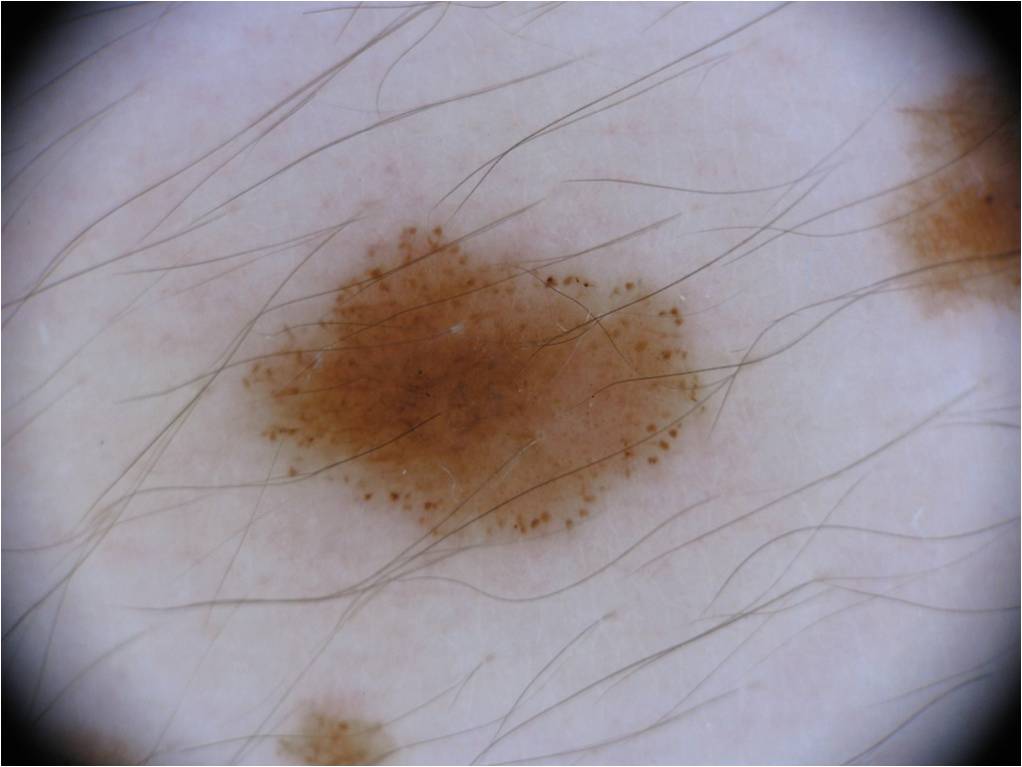Image and clinical context: This is a dermoscopic photograph of a skin lesion. A female subject approximately 15 years of age. As (left, top, right, bottom), the visible lesion spans bbox(242, 224, 704, 543). Dermoscopic review identifies pigment network and globules, with no negative network, milia-like cysts, or streaks. Impression: Clinically diagnosed as a melanocytic nevus, a benign lesion.